A skin lesion imaged with a dermatoscope · the patient says their skin reddens with sun exposure · acquired for a research image collection, with no referral diagnosis — 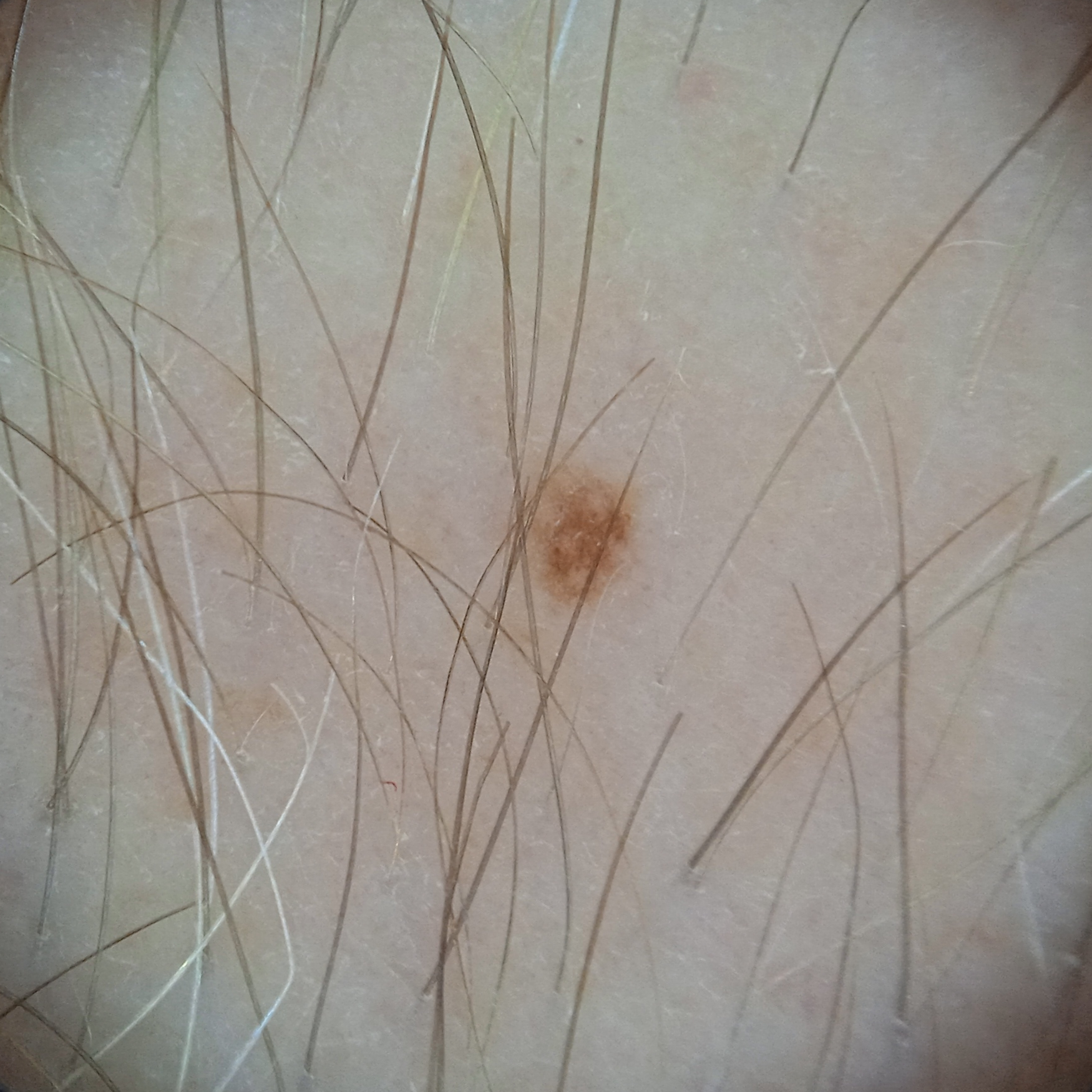<skin_lesion>
  <lesion_location>an arm</lesion_location>
  <diagnosis>
    <name>melanocytic nevus</name>
    <malignancy>benign</malignancy>
  </diagnosis>
</skin_lesion>